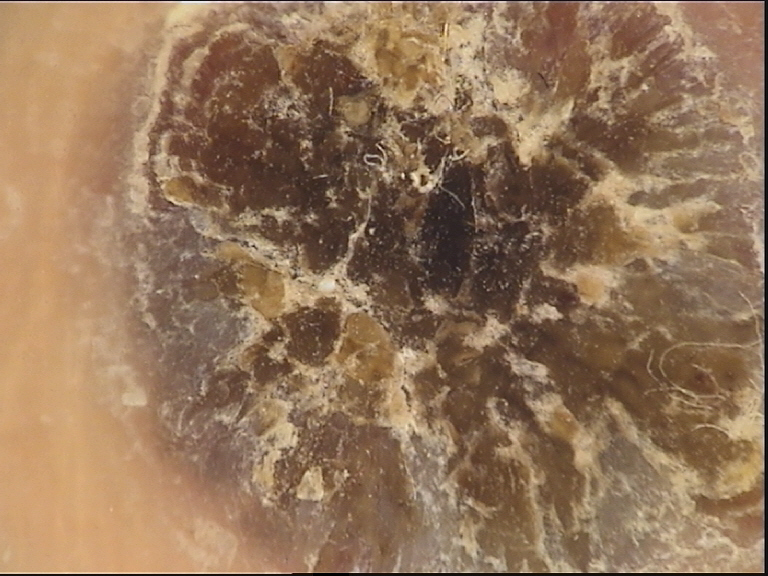Dermoscopy of a skin lesion.
Labeled as a keratinocytic, benign lesion — a seborrheic keratosis.